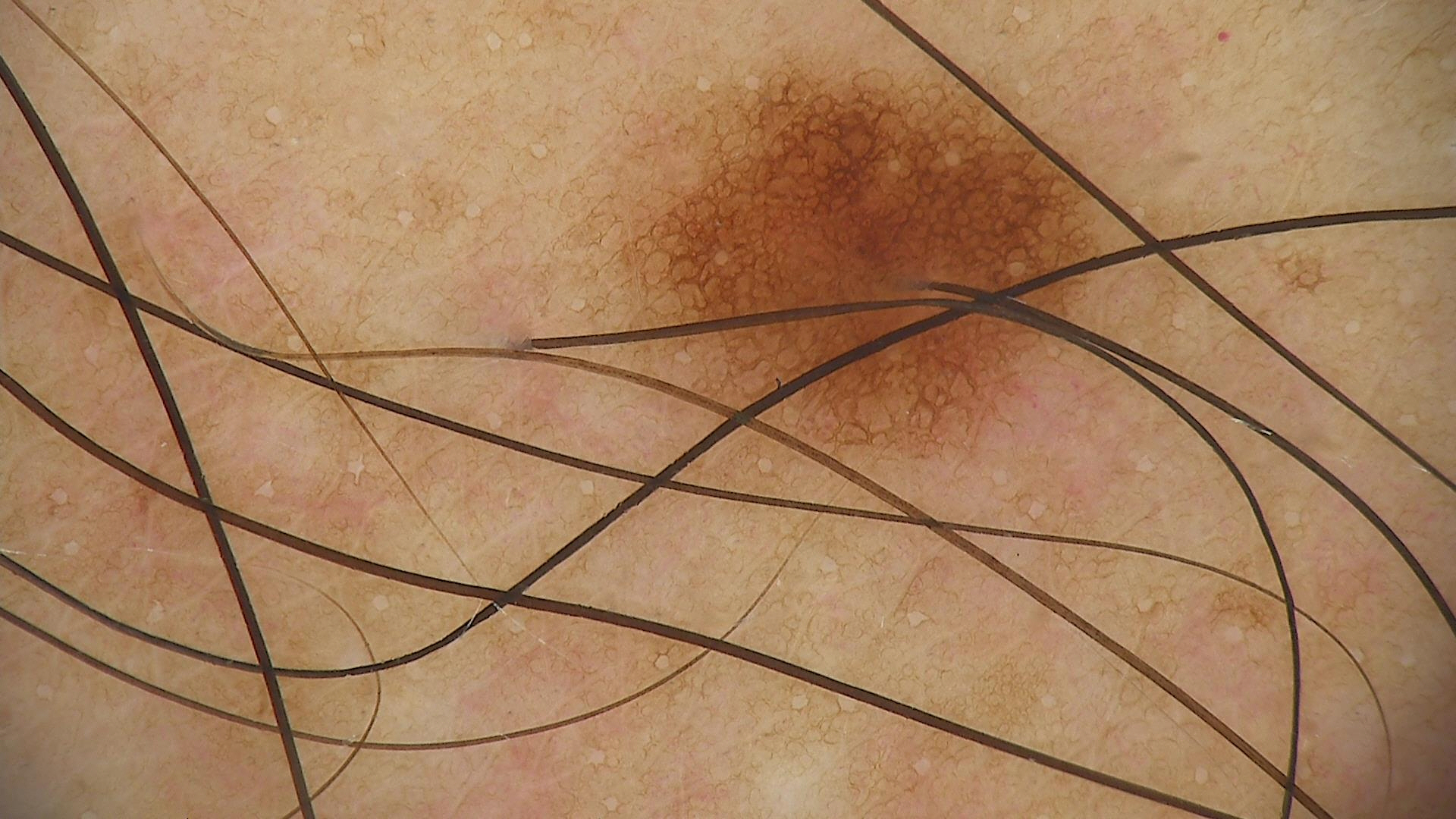• modality: dermoscopy
• assessment: dysplastic junctional nevus (expert consensus)